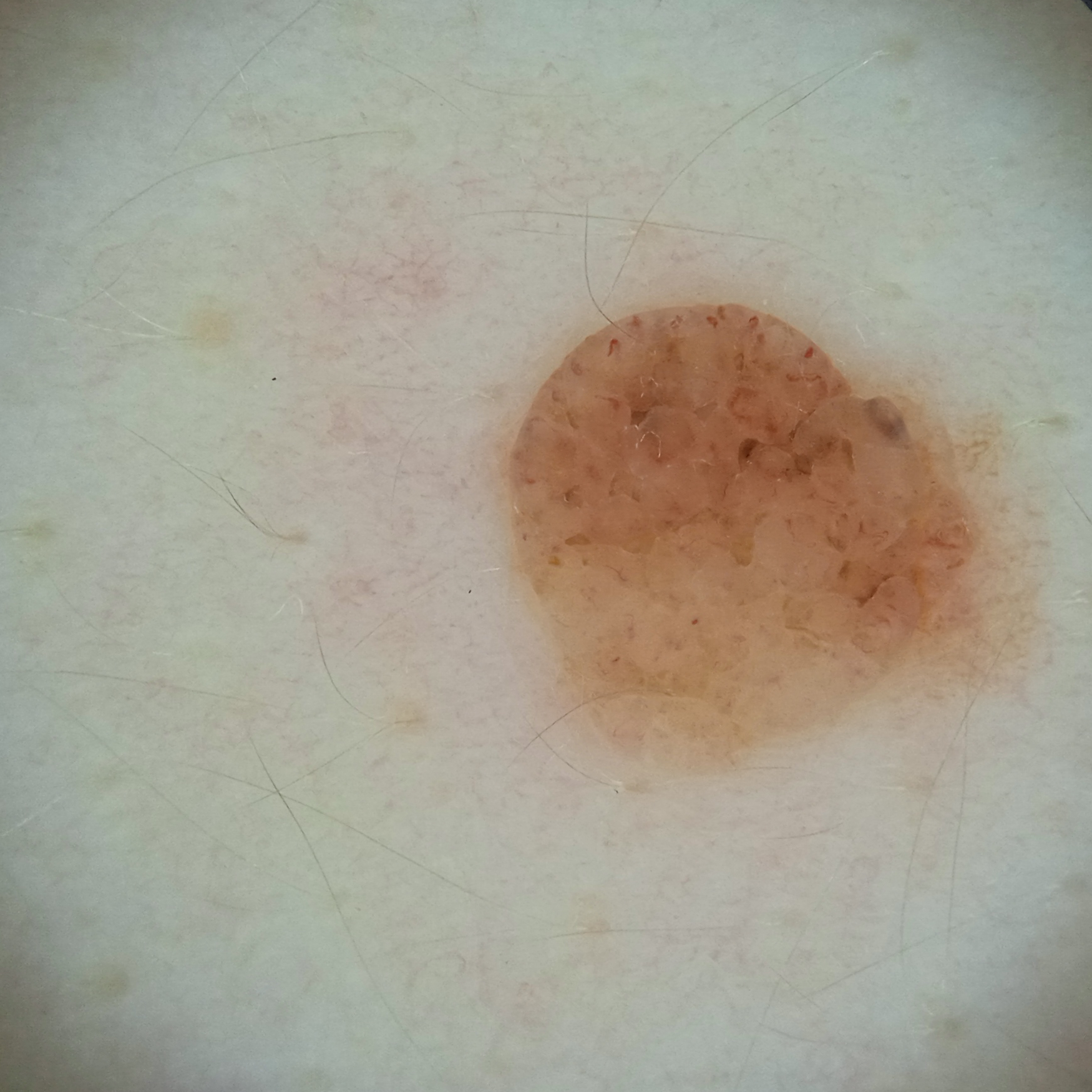On a questionnaire the patient reported a history of sunbed use. Collected as part of a research study, without a referral diagnosis. A female patient aged 26. The patient says their skin reddens with sun exposure. A skin lesion imaged with a dermatoscope. The patient describes having numerous moles. The lesion is located on the back. Measuring roughly 5.5 mm. Four dermatologists reviewed the lesion; the consensus was a melanocytic nevus; all four reviewers agreed.